A clinical photograph showing a skin lesion in context · a female patient aged around 85 or older: 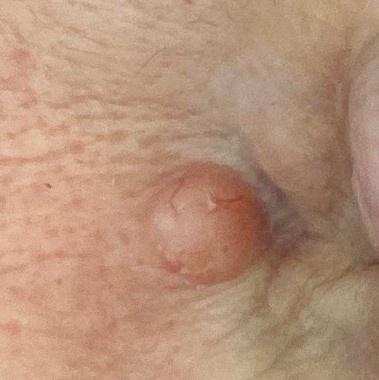body site=the head or neck
diagnosis=Basal cell carcinoma (biopsy-proven)